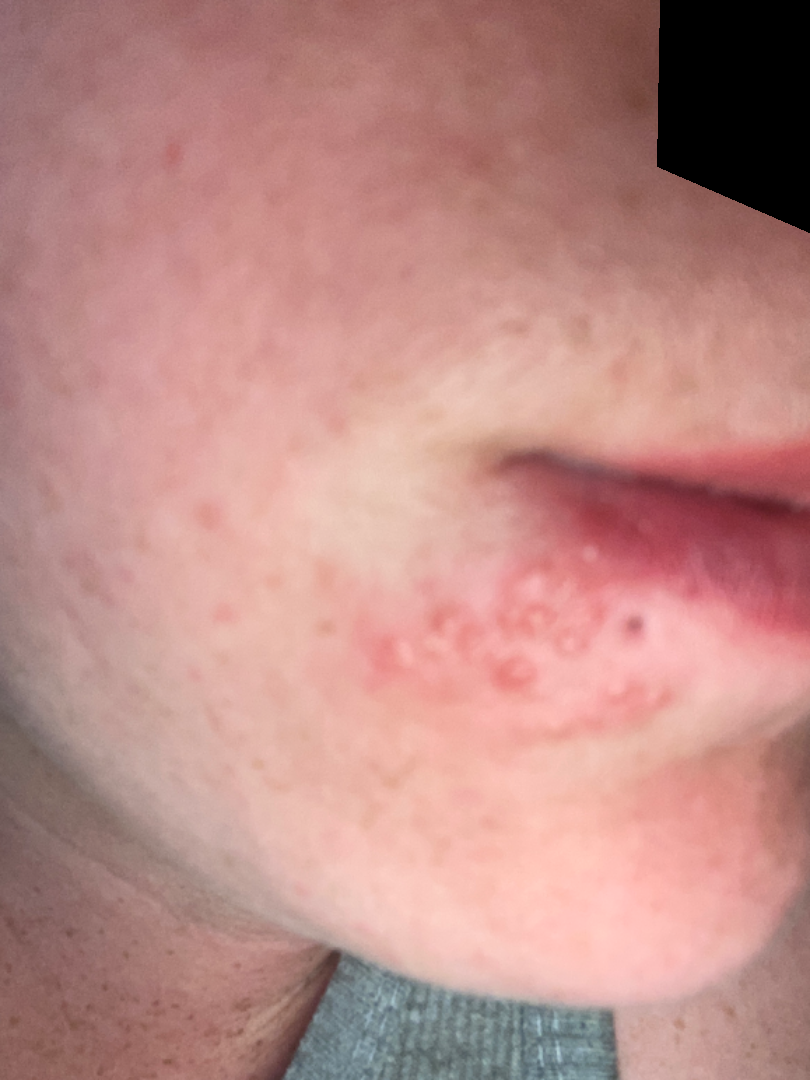<report>
<symptoms>burning</symptoms>
<duration>about one day</duration>
<texture>raised or bumpy</texture>
<systemic_symptoms>mouth sores</systemic_symptoms>
<shot_type>close-up</shot_type>
<differential>
  <Herpes Simplex>0.54</Herpes Simplex>
  <Impetigo>0.23</Impetigo>
  <Perioral Dermatitis>0.23</Perioral Dermatitis>
</differential>
</report>